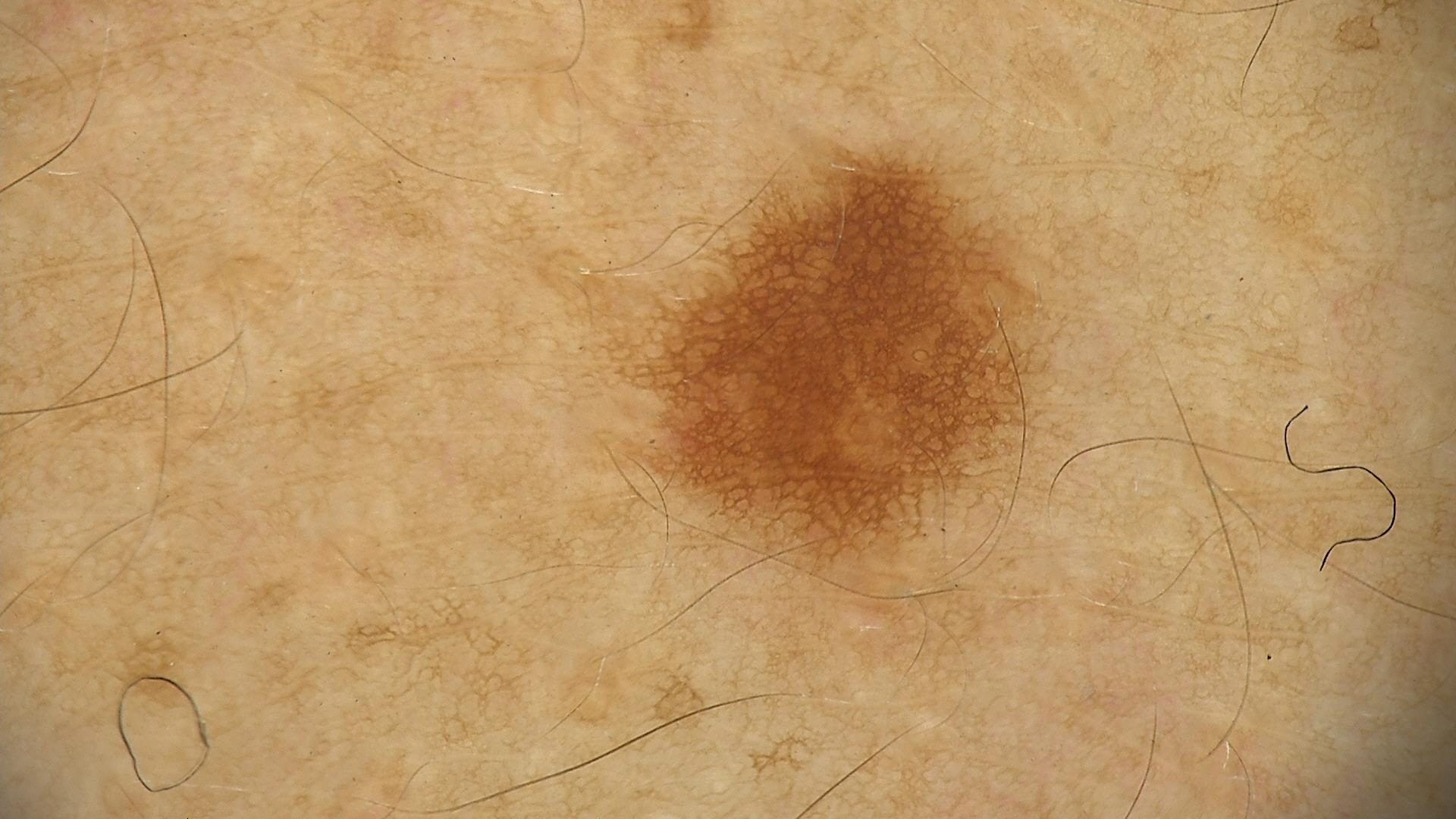Classified as a benign lesion — a dysplastic junctional nevus.